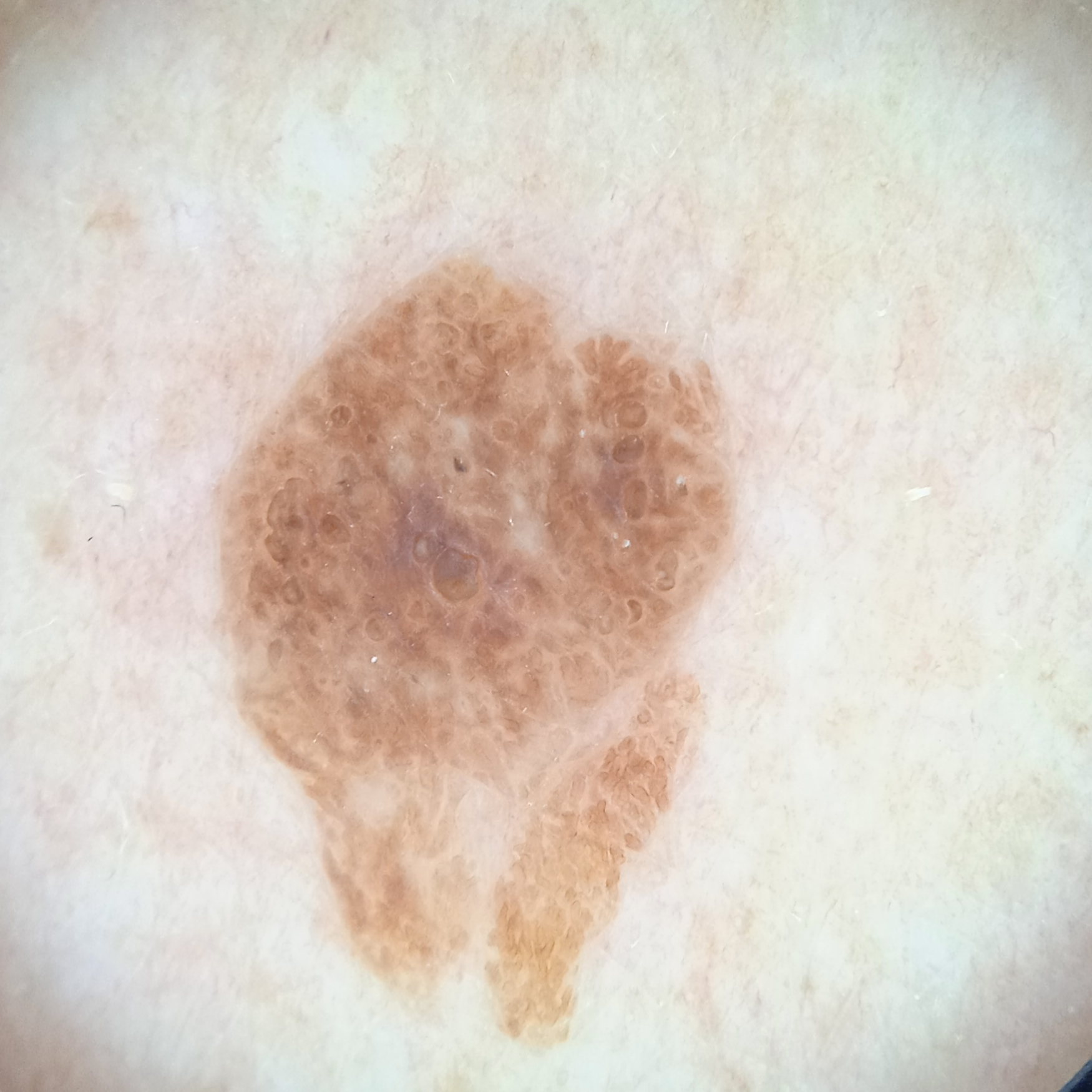Case summary: The patient says their skin tans without first burning. Acquired for a research image collection, with no referral diagnosis. Dermoscopy of a skin lesion. A male subject age 72. The patient describes having a moderate number of moles. By self-report, no prior organ transplant and no sunbed use. The lesion is on the back. The lesion is about 9.6 mm across. Impression: The dermatologists' assessment was a seborrheic keratosis.